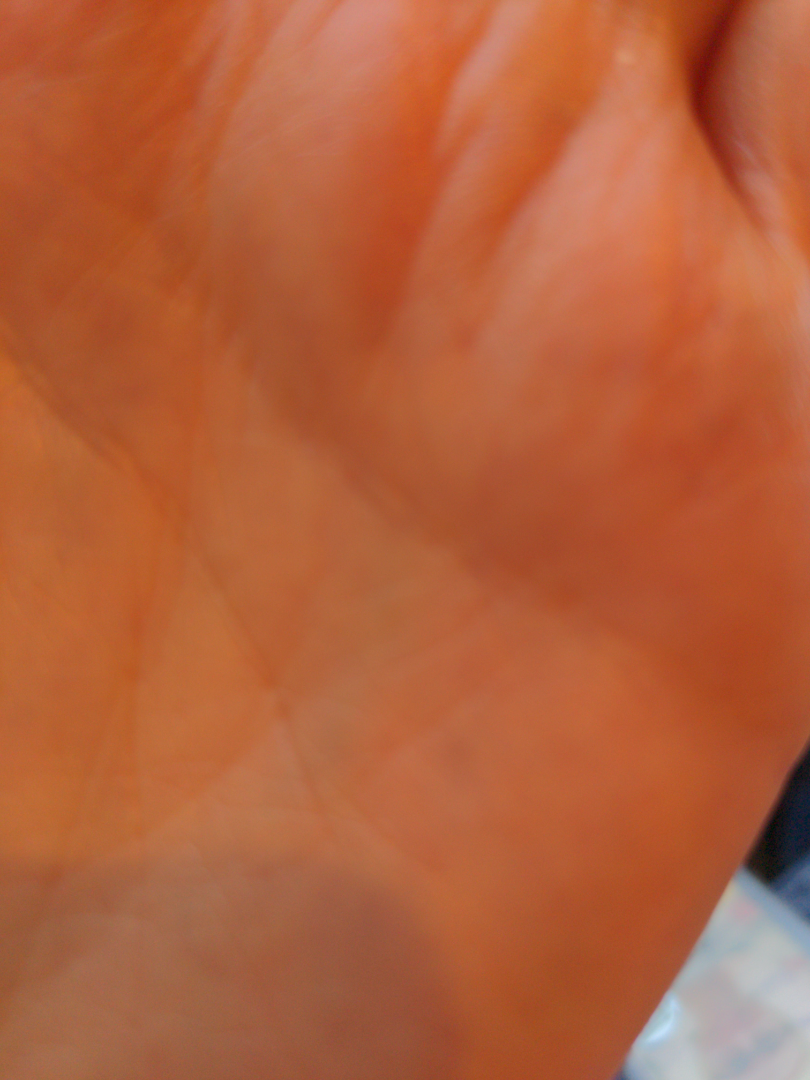Q: What was the assessment?
A: no clear pathology
Q: What is the framing?
A: at a distance